A skin lesion imaged with a dermatoscope: 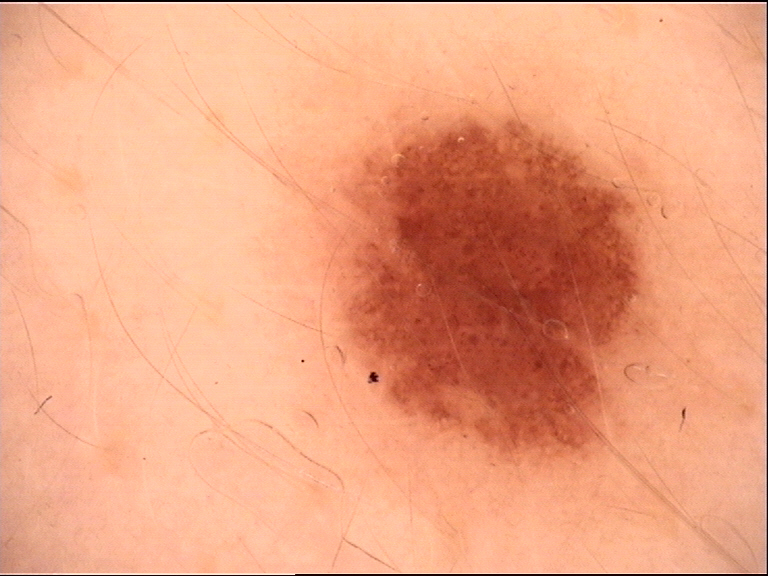assessment: junctional nevus (expert consensus).